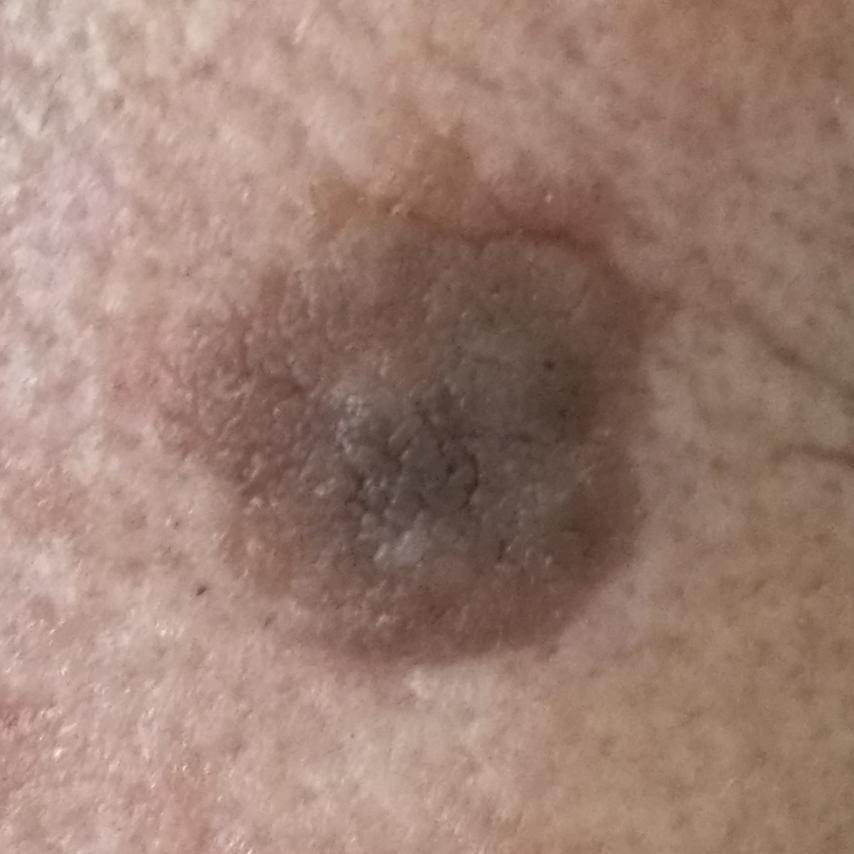A clinical photograph showing a skin lesion. A patient aged 60. The lesion is on the face. By the patient's account, the lesion itches and hurts, but has not changed and is not elevated. Consistent with a seborrheic keratosis.